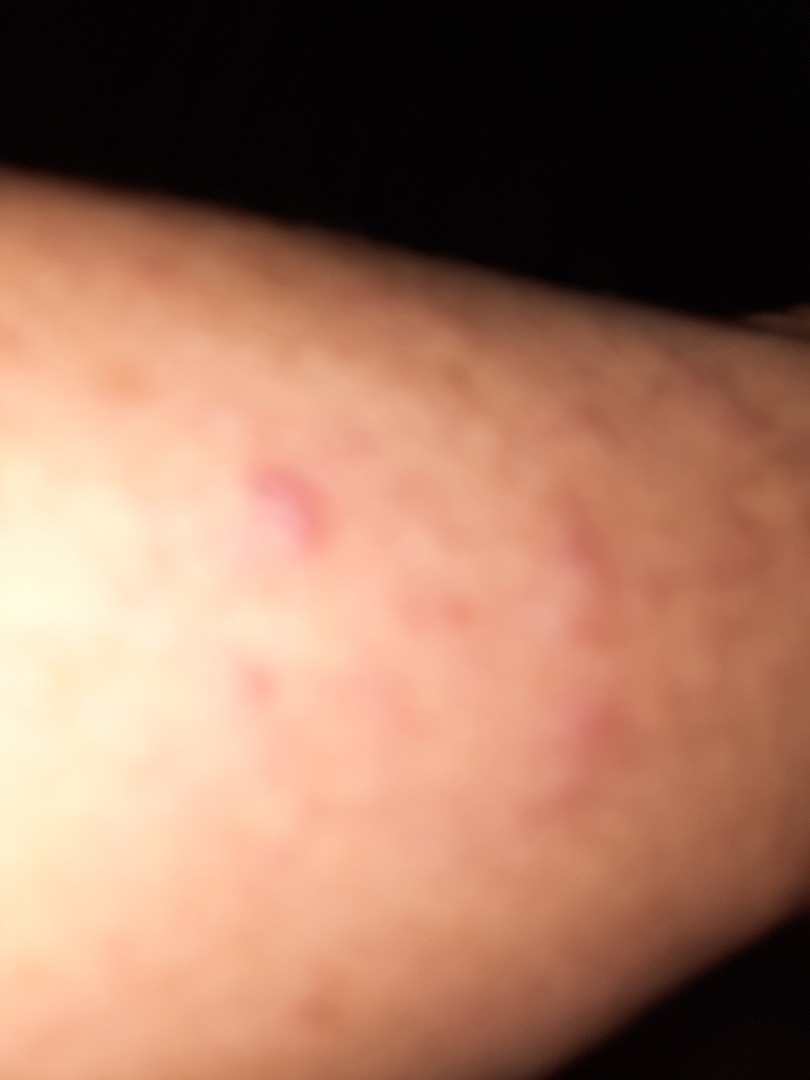The condition could not be reliably identified from the image.